Dermoscopy of a skin lesion: 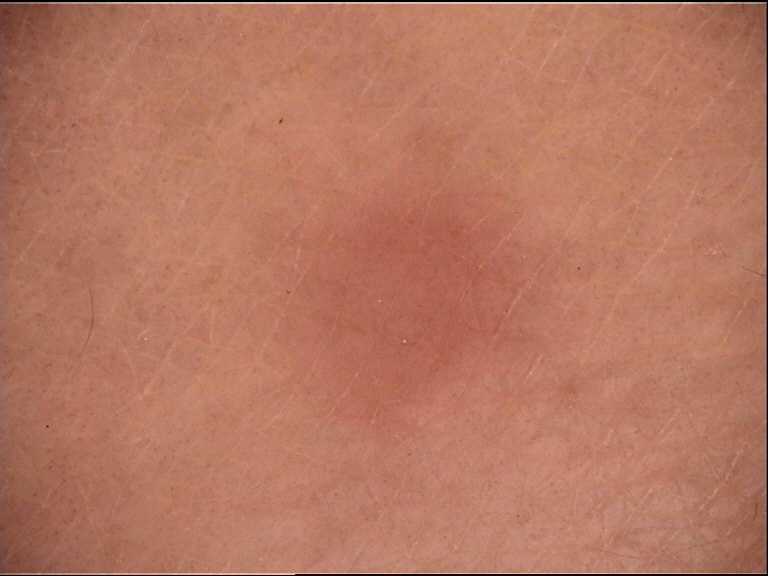classification = fibro-histiocytic | diagnostic label = dermatofibroma (expert consensus).